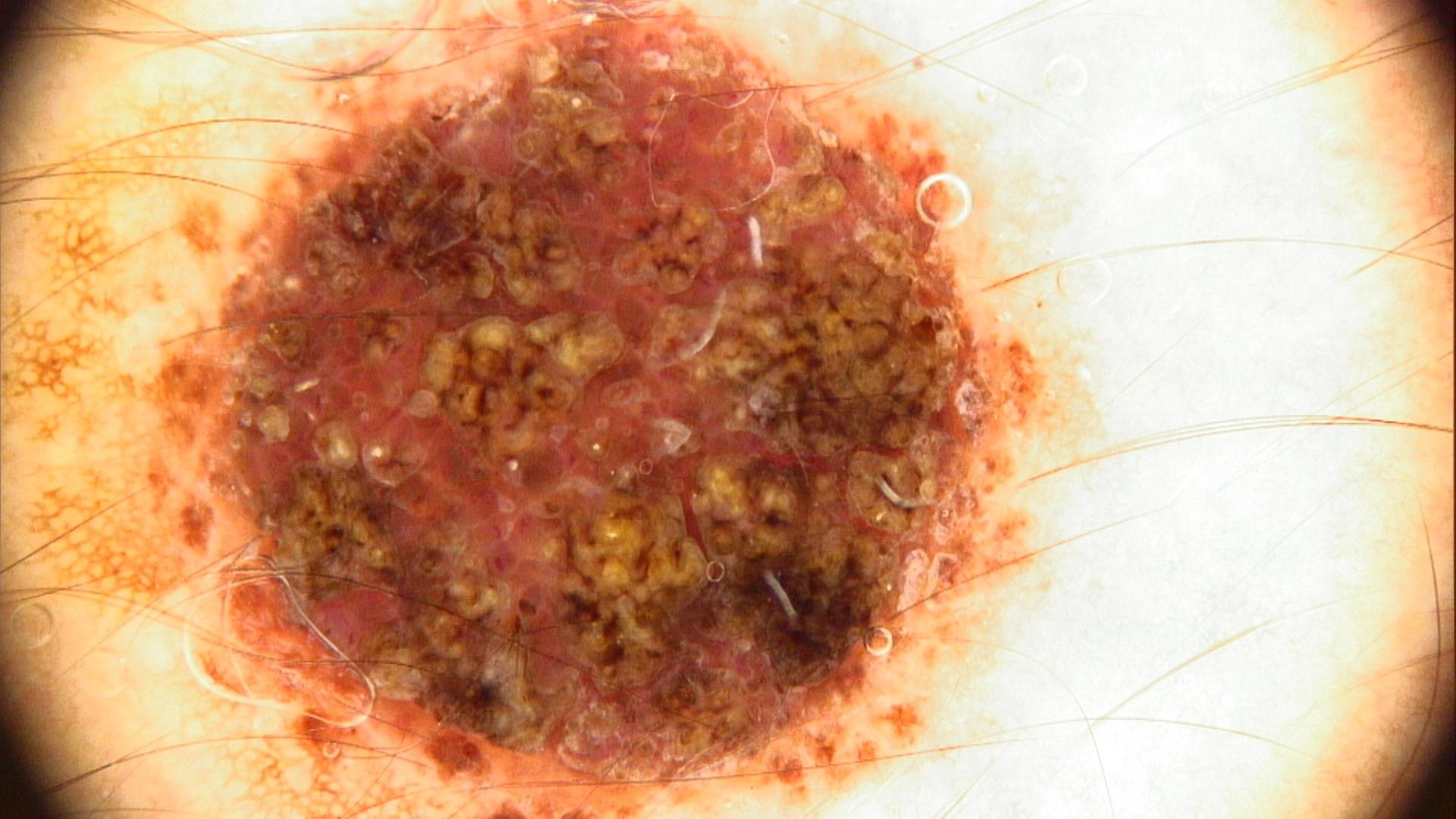imaging: dermatoscopic image, anatomic site: the trunk, diagnosis: Nevus (biopsy-proven).